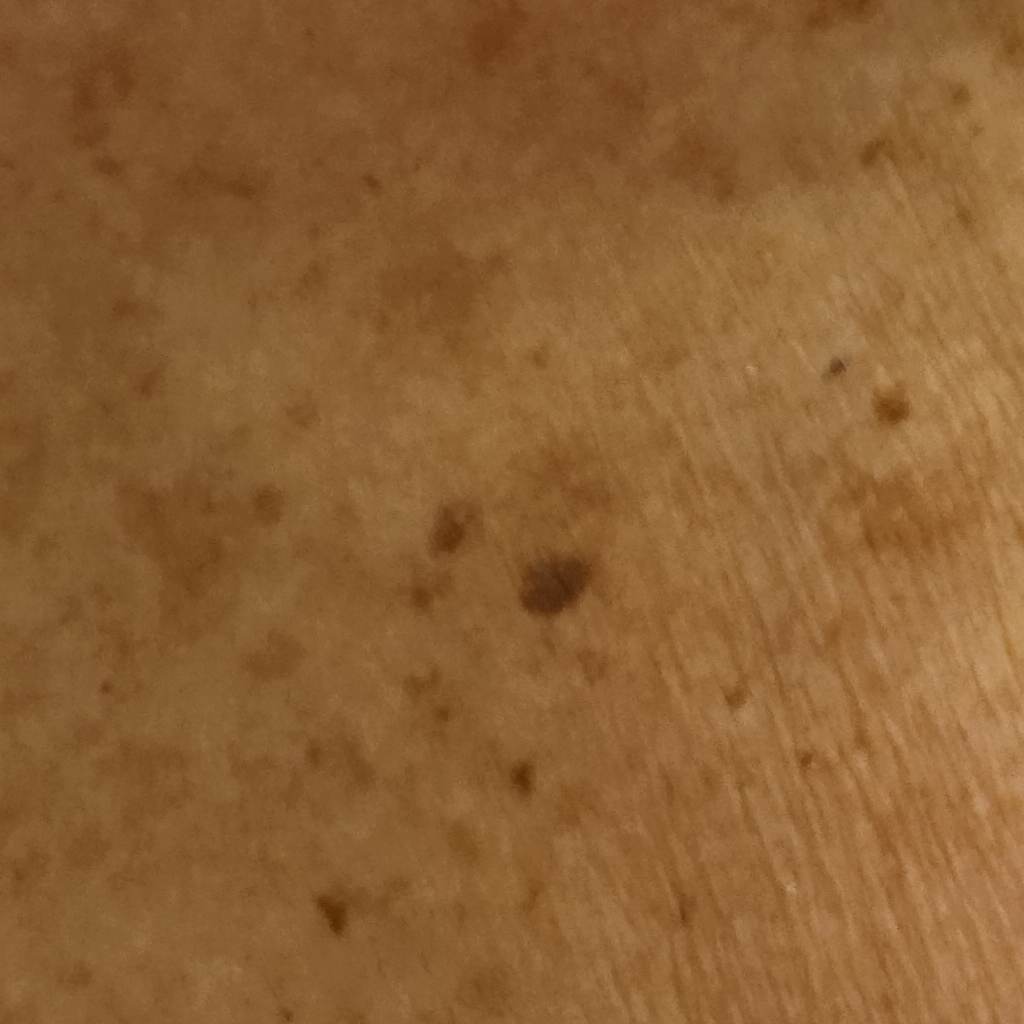Summary: The patient says their skin tans without first burning. The patient describes having few moles overall. A clinical close-up of a skin lesion. Imaged for a research study, with no referral diagnosis recorded. A female subject 84 years old. The lesion is located on the torso. The lesion is about 4.6 mm across. Conclusion: Dermatologist review favored a seborrheic keratosis.